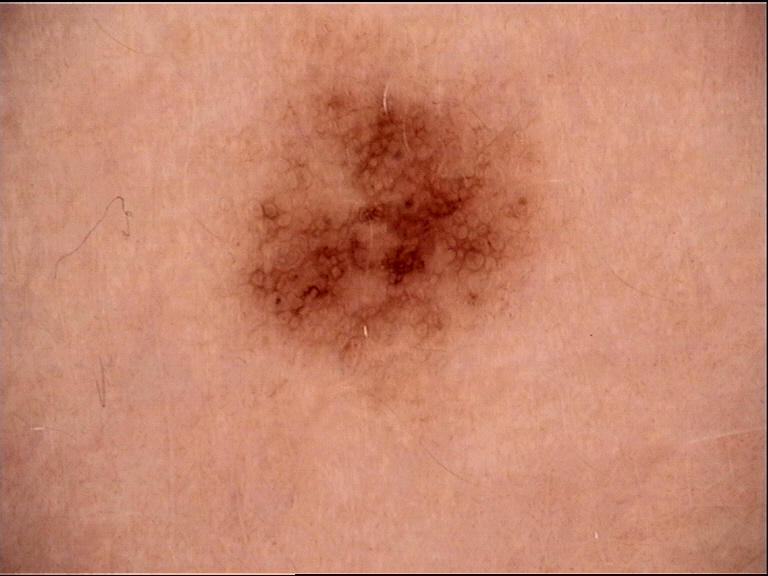label: dysplastic junctional nevus (expert consensus).